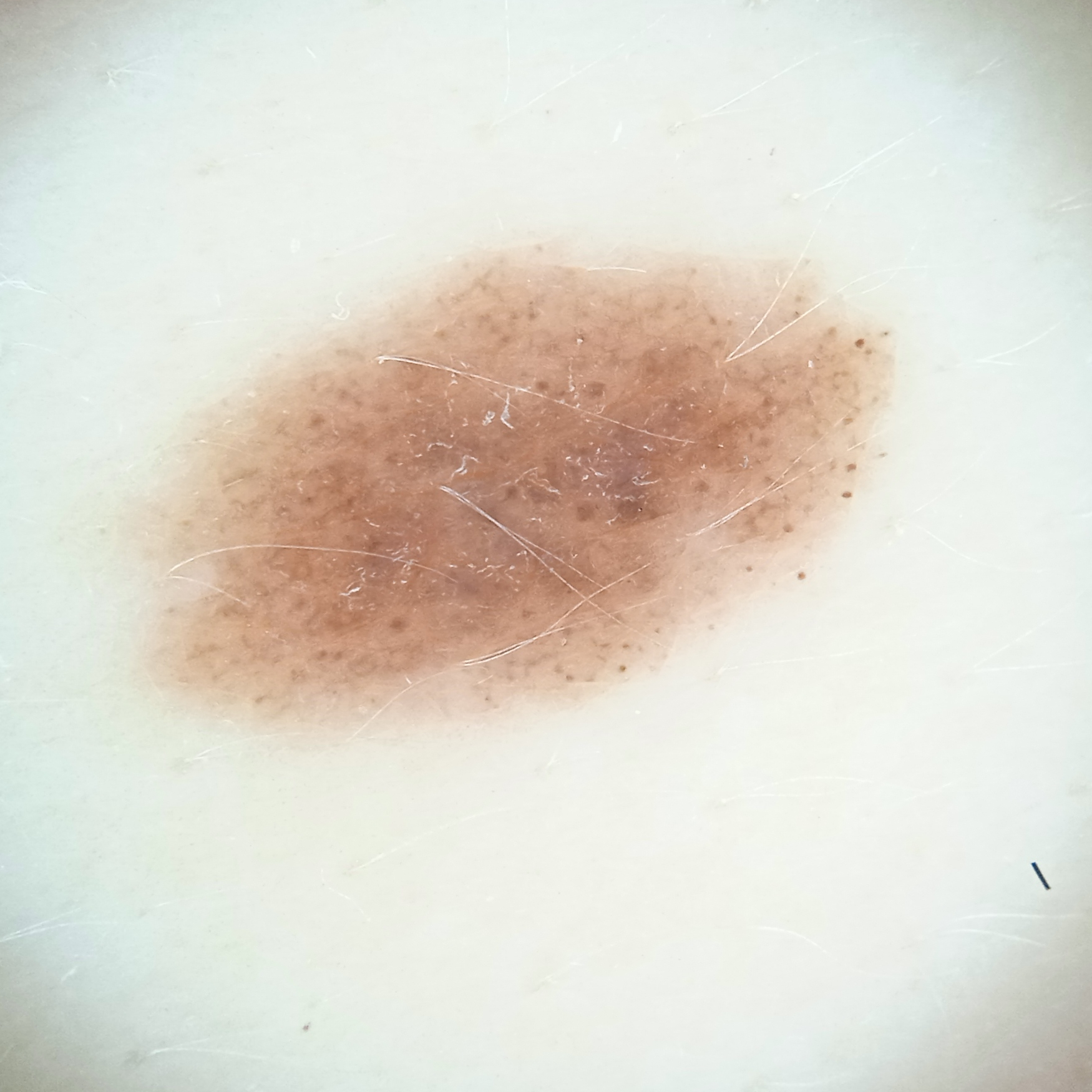Case:
– sun reaction: skin reddens with sun exposure
– referral: research study (no referral diagnosis)
– modality: dermatoscopic image
– patient: female, 27 years of age
– nevus count: a moderate number of melanocytic nevi
– size: 9.4 mm
– diagnostic label: melanocytic nevus (dermatologist consensus)